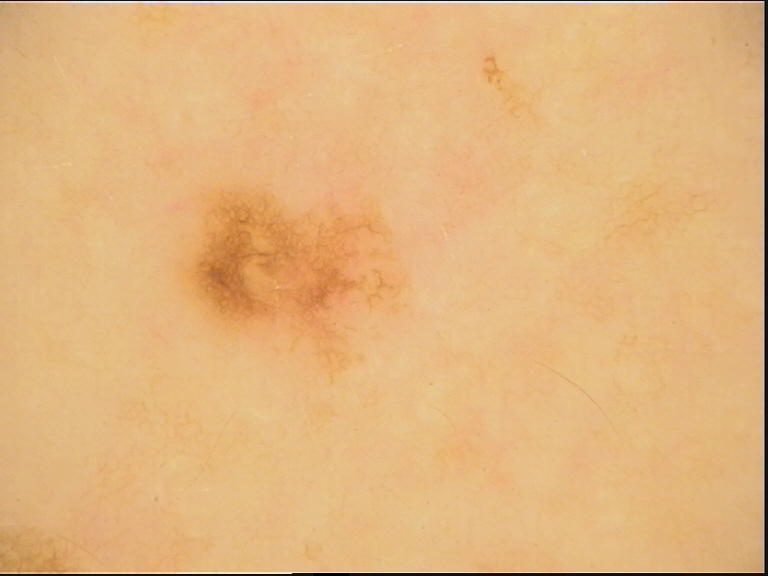– image type — dermoscopy
– diagnosis — dysplastic junctional nevus (expert consensus)